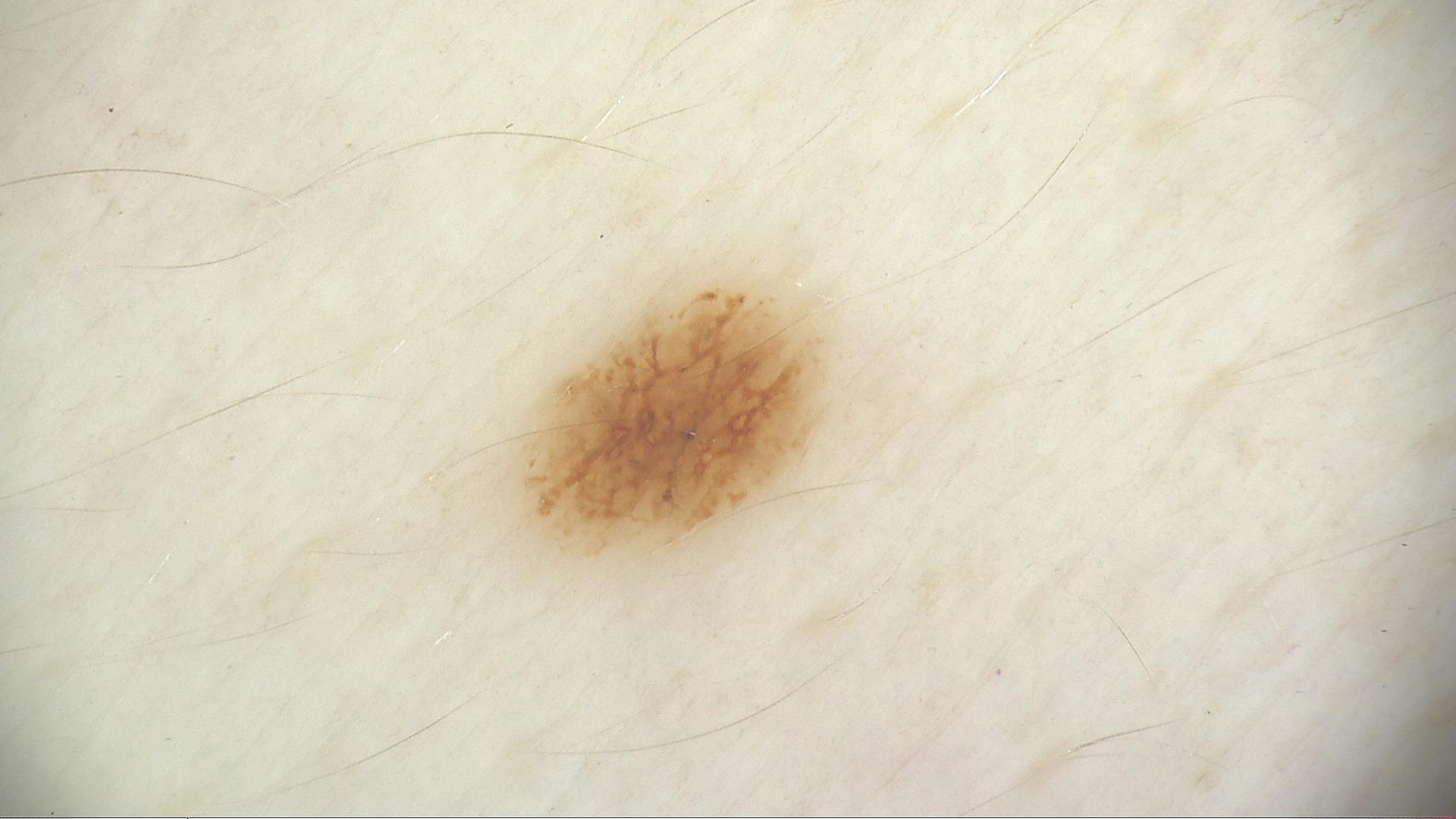{
  "image": "dermoscopy",
  "diagnosis": {
    "name": "dysplastic junctional nevus",
    "code": "jd",
    "malignancy": "benign",
    "super_class": "melanocytic",
    "confirmation": "expert consensus"
  }
}